A dermoscopic close-up of a skin lesion.
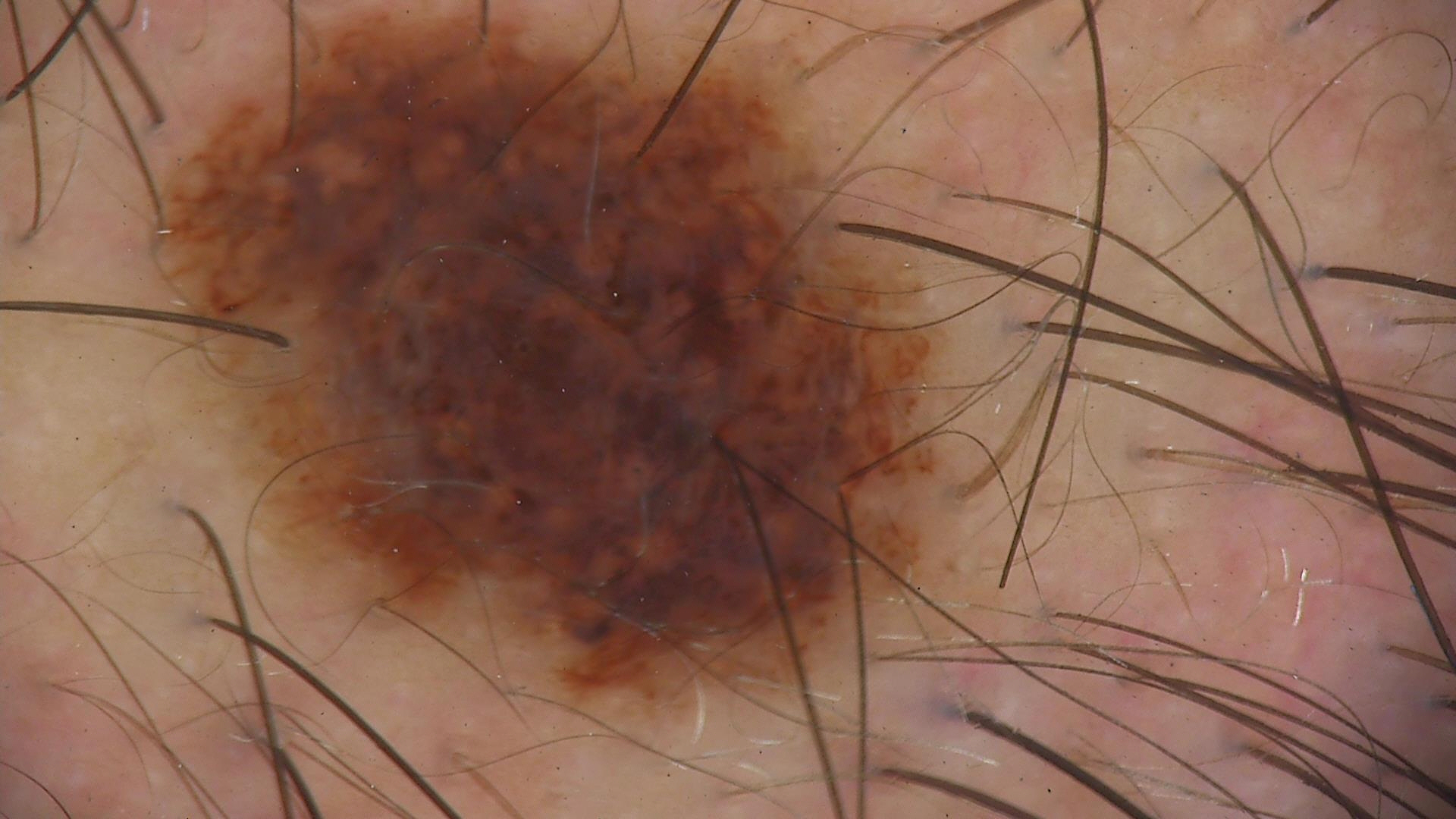diagnosis = dysplastic compound nevus (expert consensus).